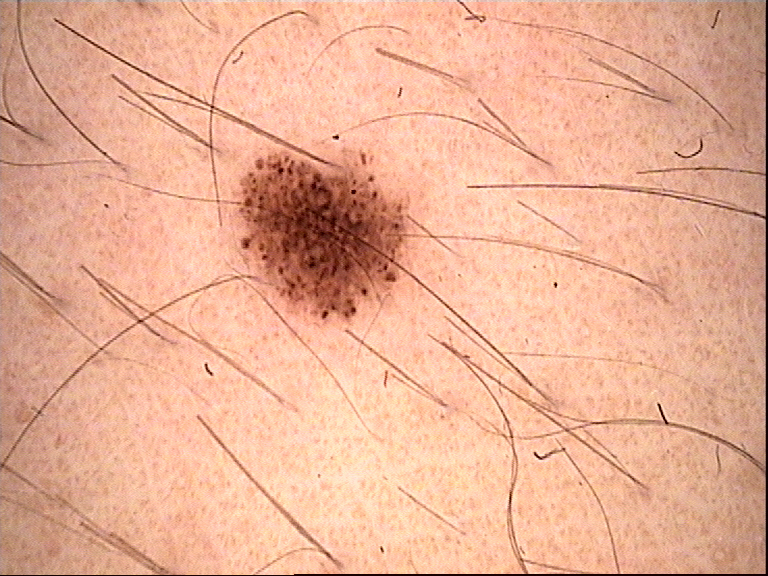image = dermatoscopy; assessment = dysplastic junctional nevus (expert consensus).